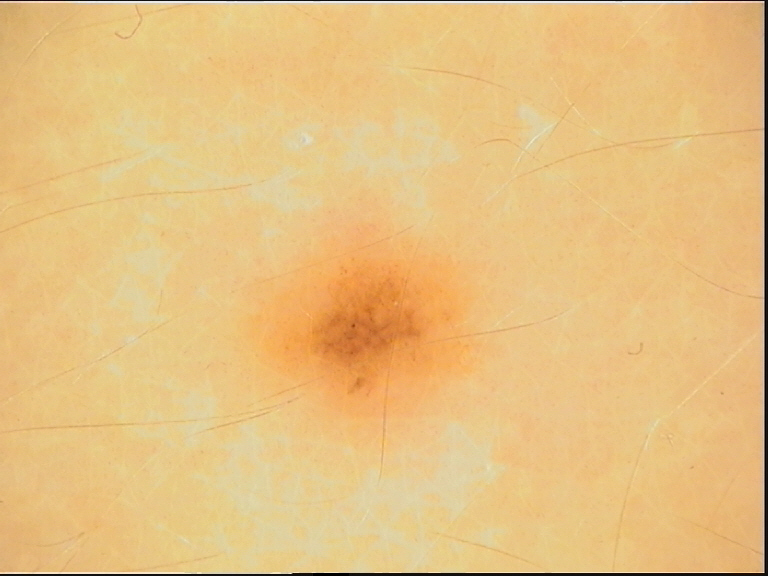Findings:
* imaging · dermoscopy
* diagnostic label · dysplastic junctional nevus (expert consensus)